The subject is 50–59, female; this image was taken at a distance; the back of the torso is involved: 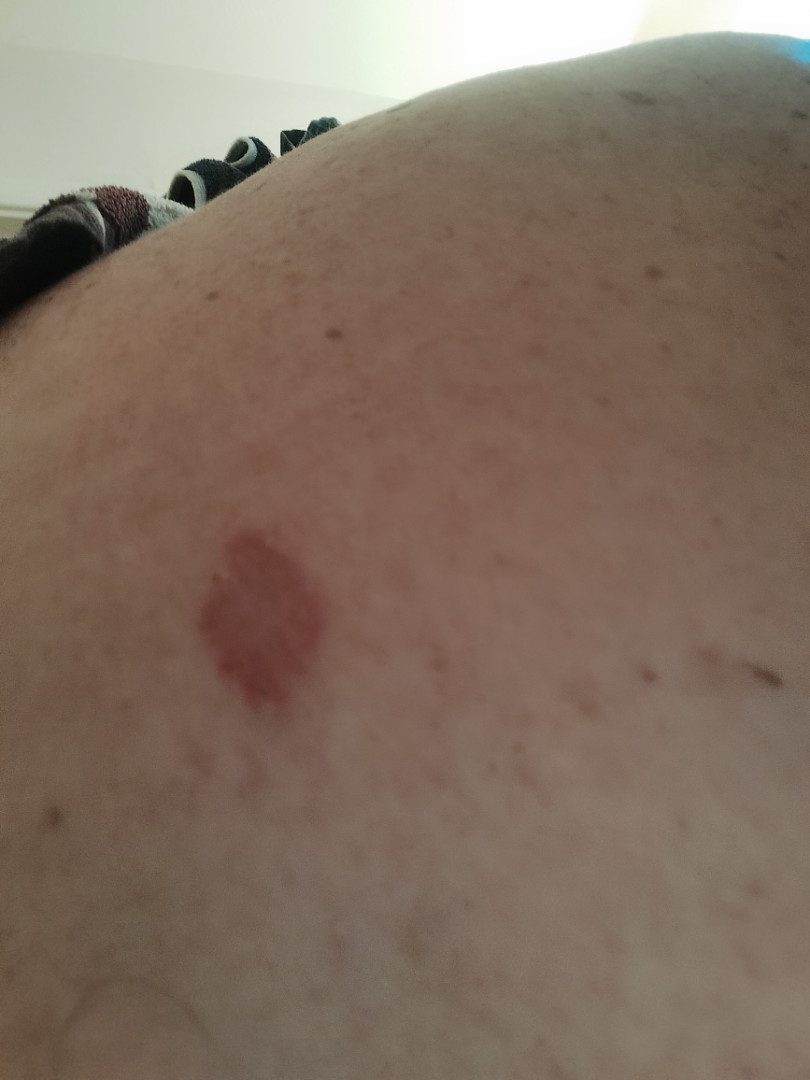Q: What symptoms does the patient report?
A: bothersome appearance
Q: How does the lesion feel?
A: rough or flaky
Q: Fitzpatrick or Monk tone?
A: Fitzpatrick skin type II
Q: What is the differential diagnosis?
A: most likely Basal Cell Carcinoma; with consideration of SCC/SCCIS; less likely is Eczema